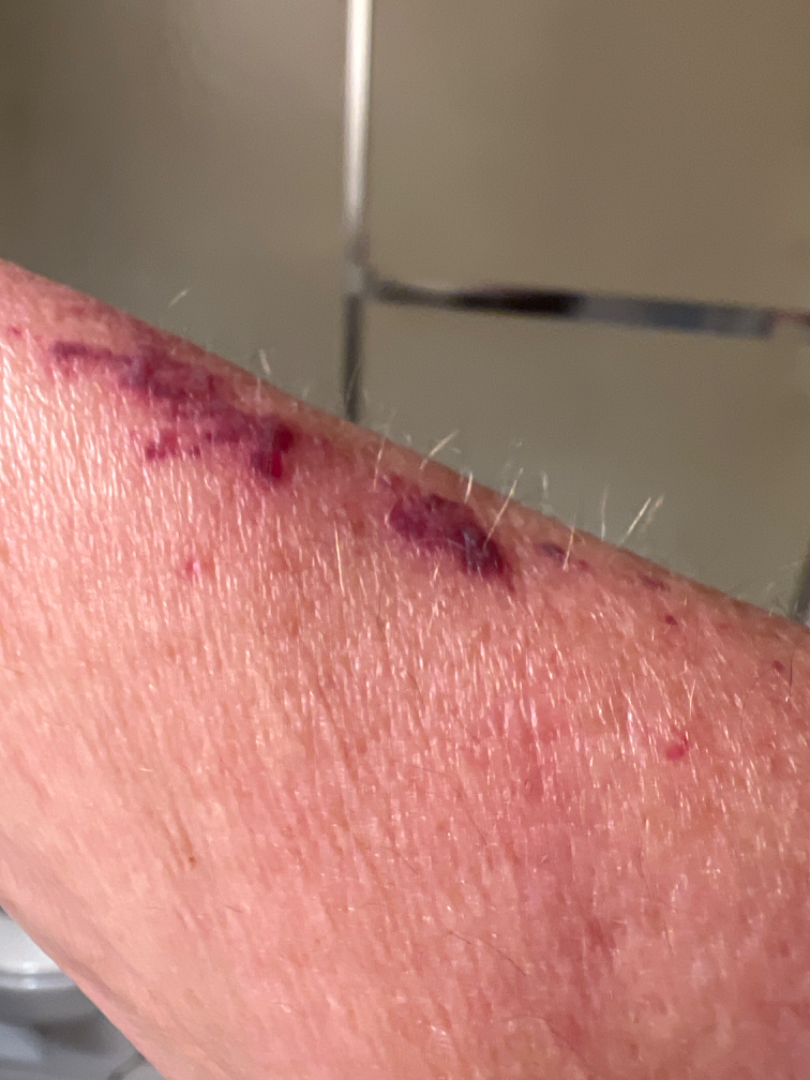| feature | finding |
|---|---|
| assessment | could not be assessed |